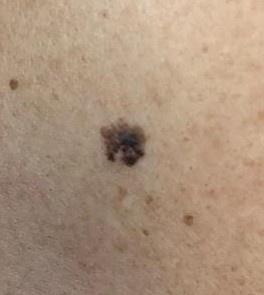Case:
* diagnosis · Seborrheic keratosis (biopsy-proven)